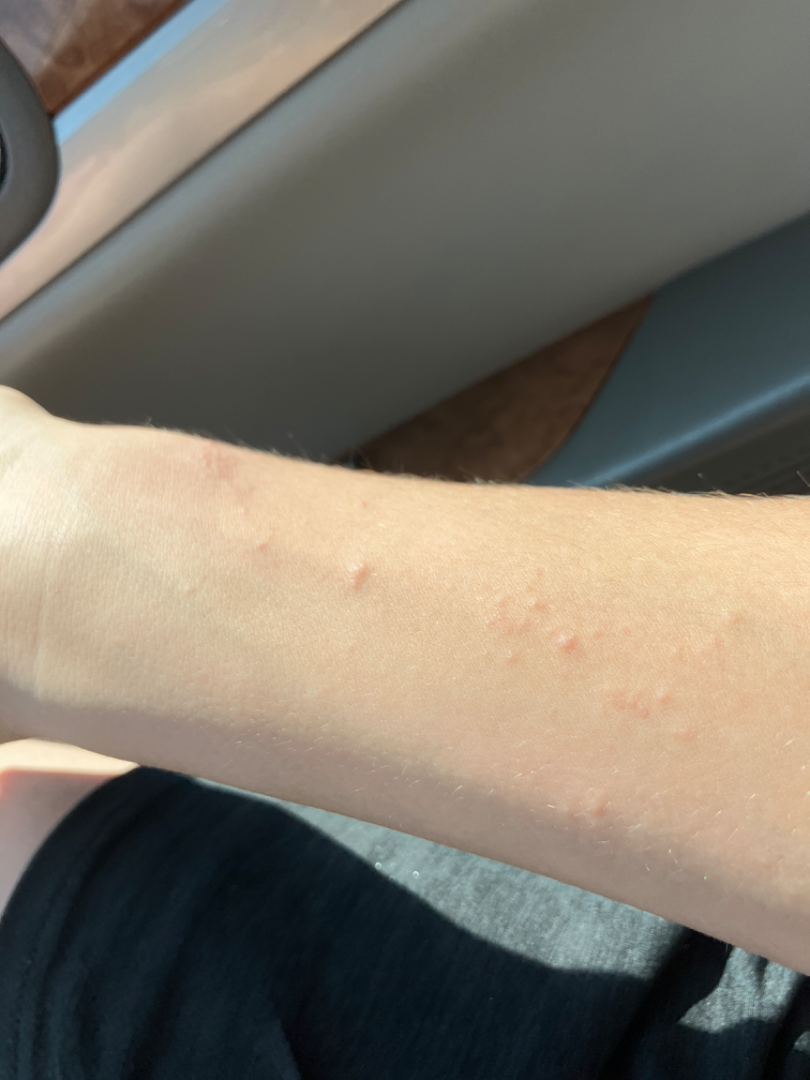constitutional symptoms — none reported | view — at an angle | lesion symptoms — itching | skin tone — Fitzpatrick skin type II | symptom duration — about one day | patient describes the issue as — a rash | lesion texture — raised or bumpy | location — arm | assessment — most consistent with Allergic Contact Dermatitis.